A dermatoscopic image of a skin lesion.
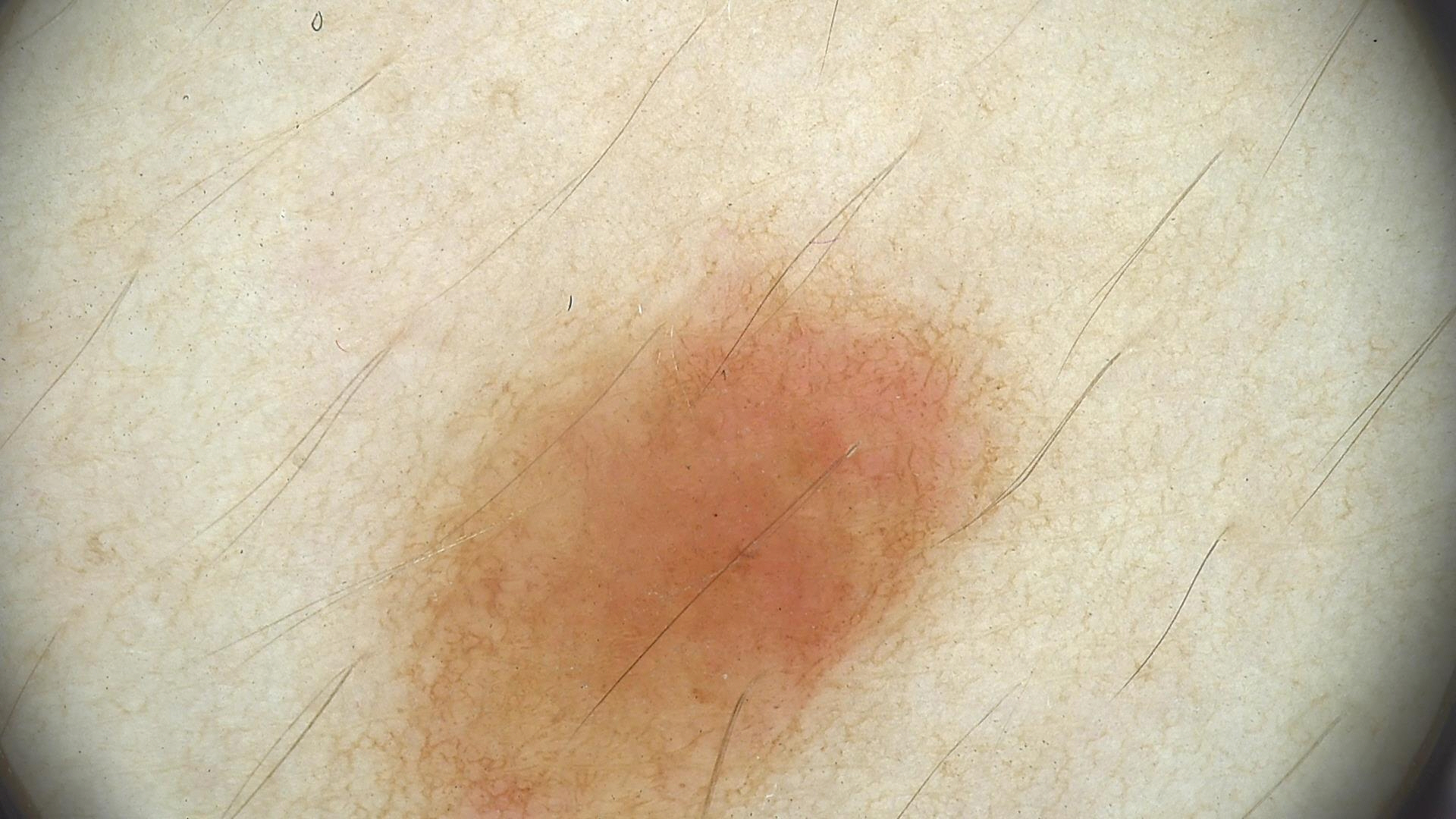Impression:
Labeled as a benign lesion — a dysplastic junctional nevus.